A dermoscopic close-up of a skin lesion:
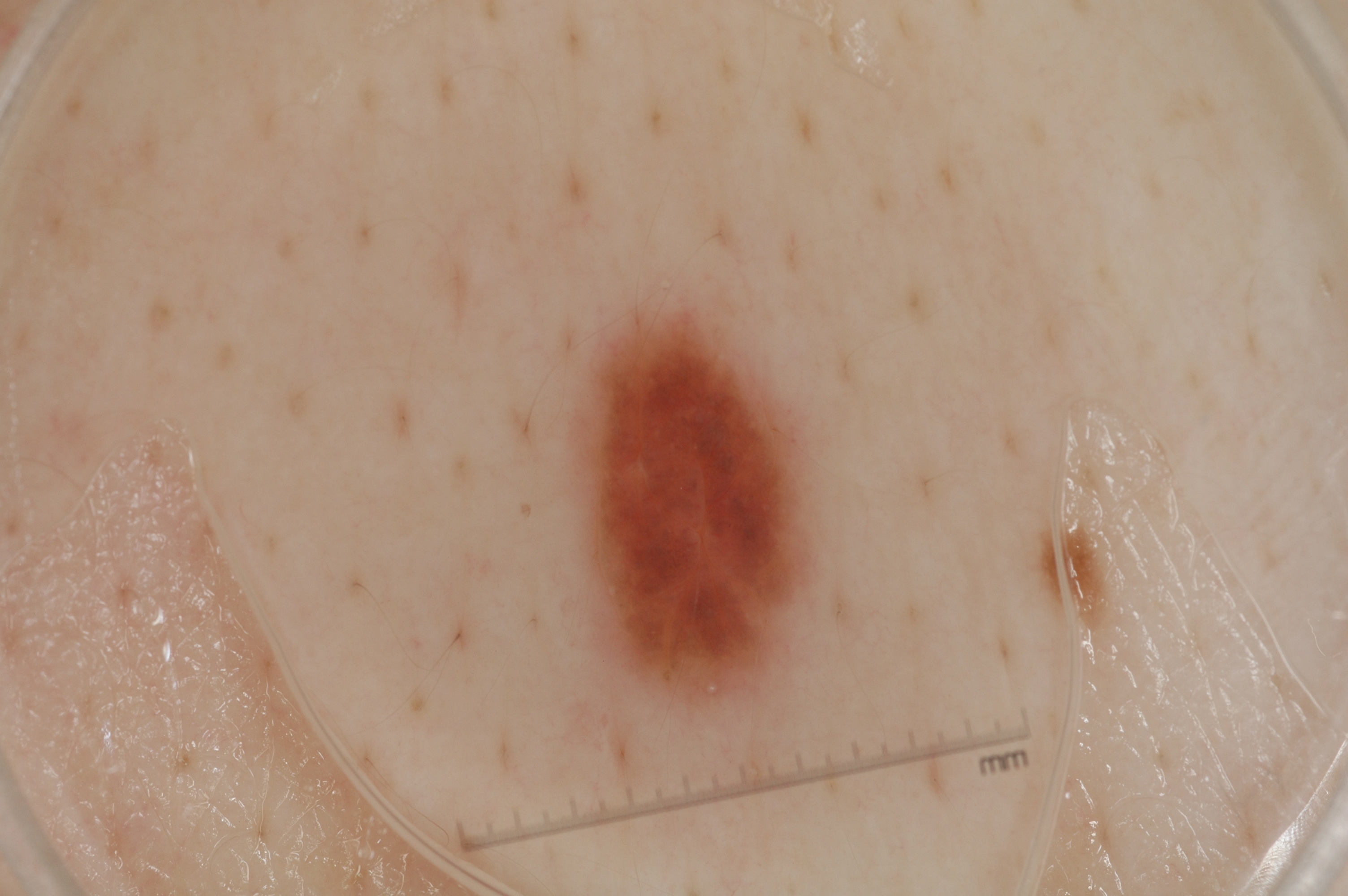  lesion_extent:
    approx_field_fraction_pct: 6
  dermoscopic_features:
    present:
      - milia-like cysts
    absent:
      - negative network
      - pigment network
      - streaks
  lesion_location:
    bbox_xyxy:
      - 579
      - 301
      - 811
      - 700
  diagnosis:
    name: melanocytic nevus
    malignancy: benign
    lineage: melanocytic
    provenance: clinical